An image taken at a distance; the lesion involves the leg.
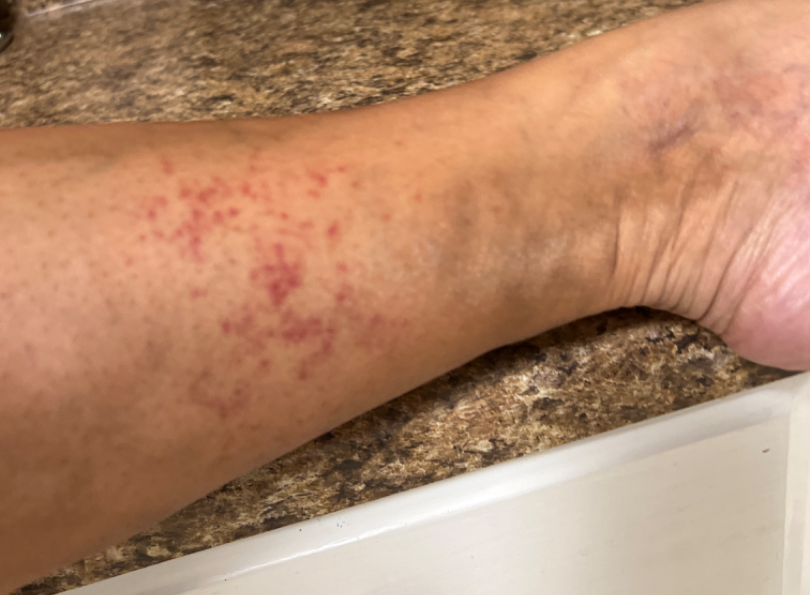The skin findings could not be characterized from the image.